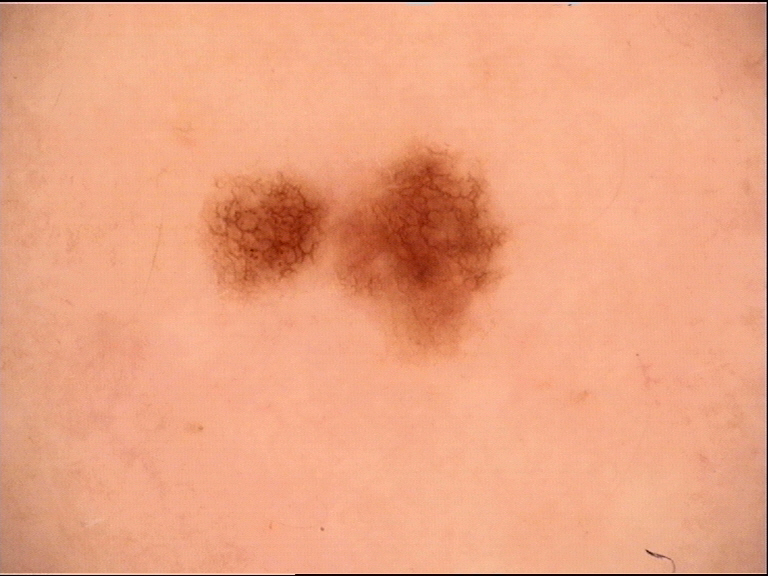label: dysplastic junctional nevus (expert consensus).